Reported lesion symptoms include itching · this image was taken at a distance · the contributor is 18–29, female · the affected area is the back of the hand, leg and arm · texture is reported as raised or bumpy · the patient described the issue as a rash: 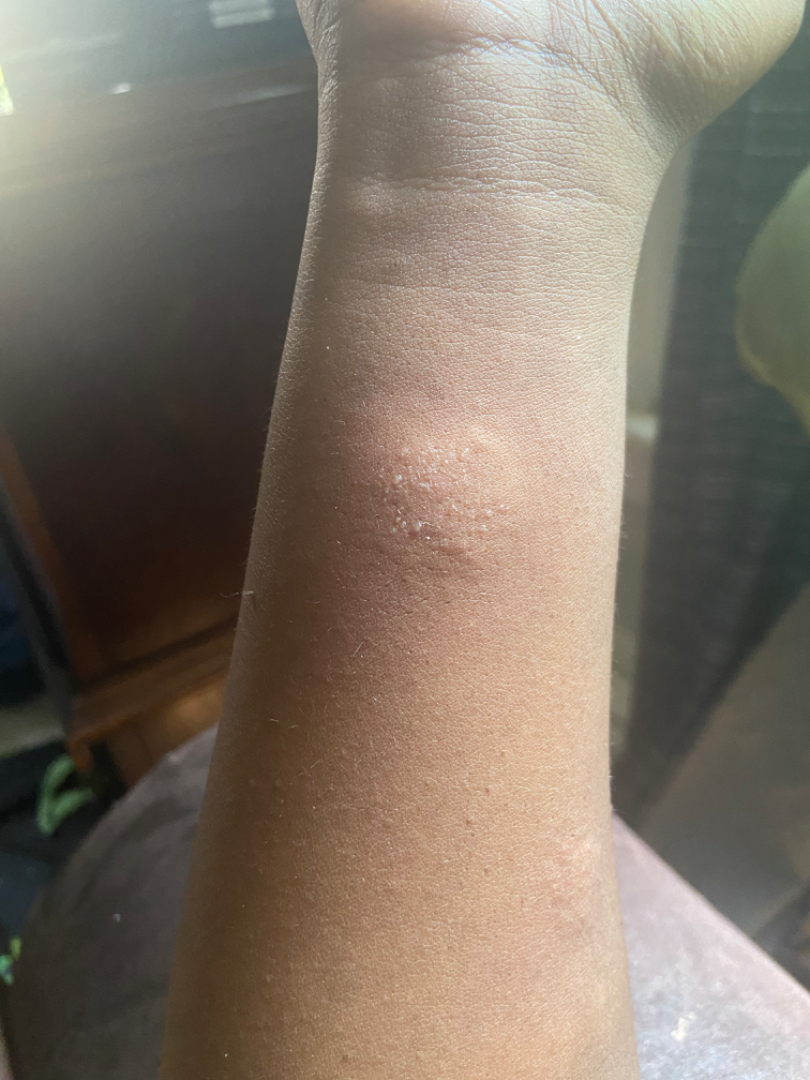Review:
The reviewing panel's impression was: Abscess (possible); Impetigo (possible); Insect Bite (possible).